The patient says their skin reddens painfully with sun exposure; collected as part of a research study, without a referral diagnosis; a clinical close-up of a skin lesion; a moderate number of moles by the patient's own estimate:
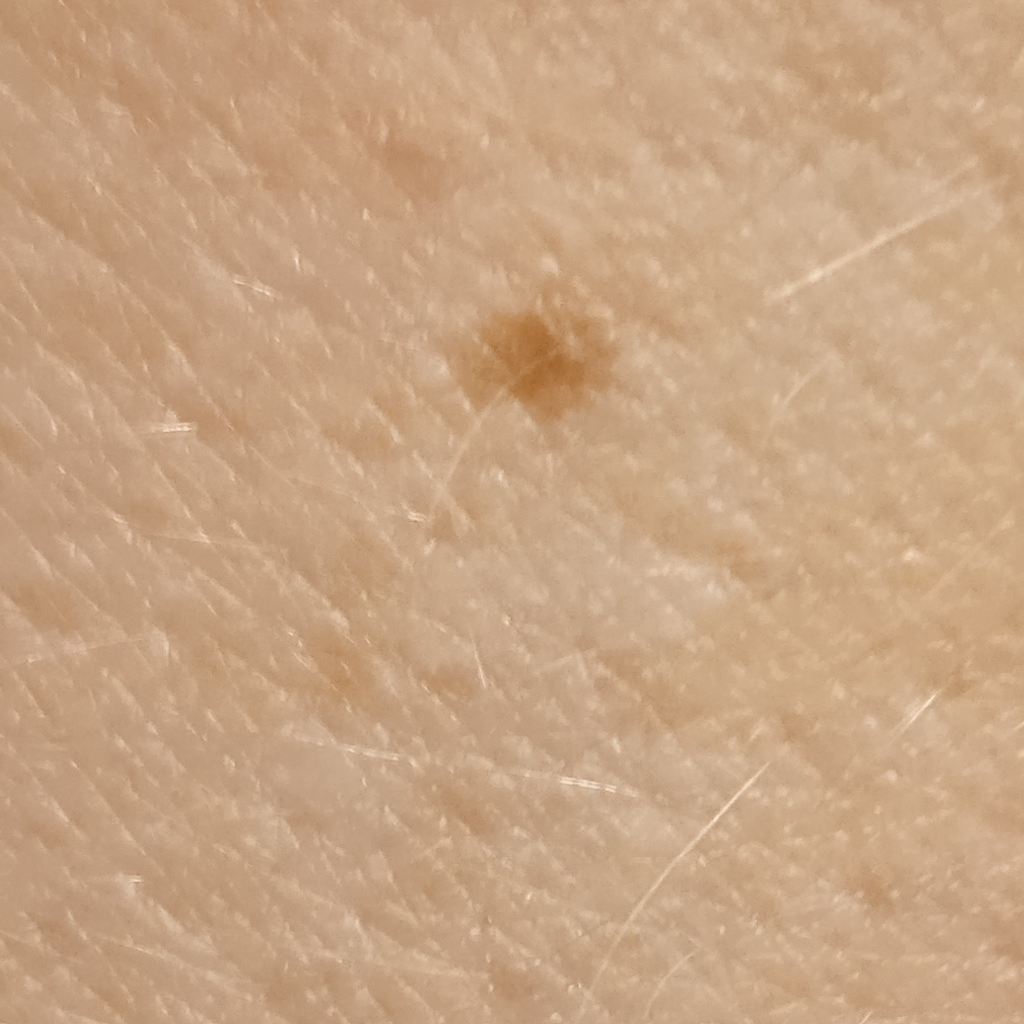The lesion involves an arm. Measuring roughly 2 mm. The diagnostic impression was a melanocytic nevus.